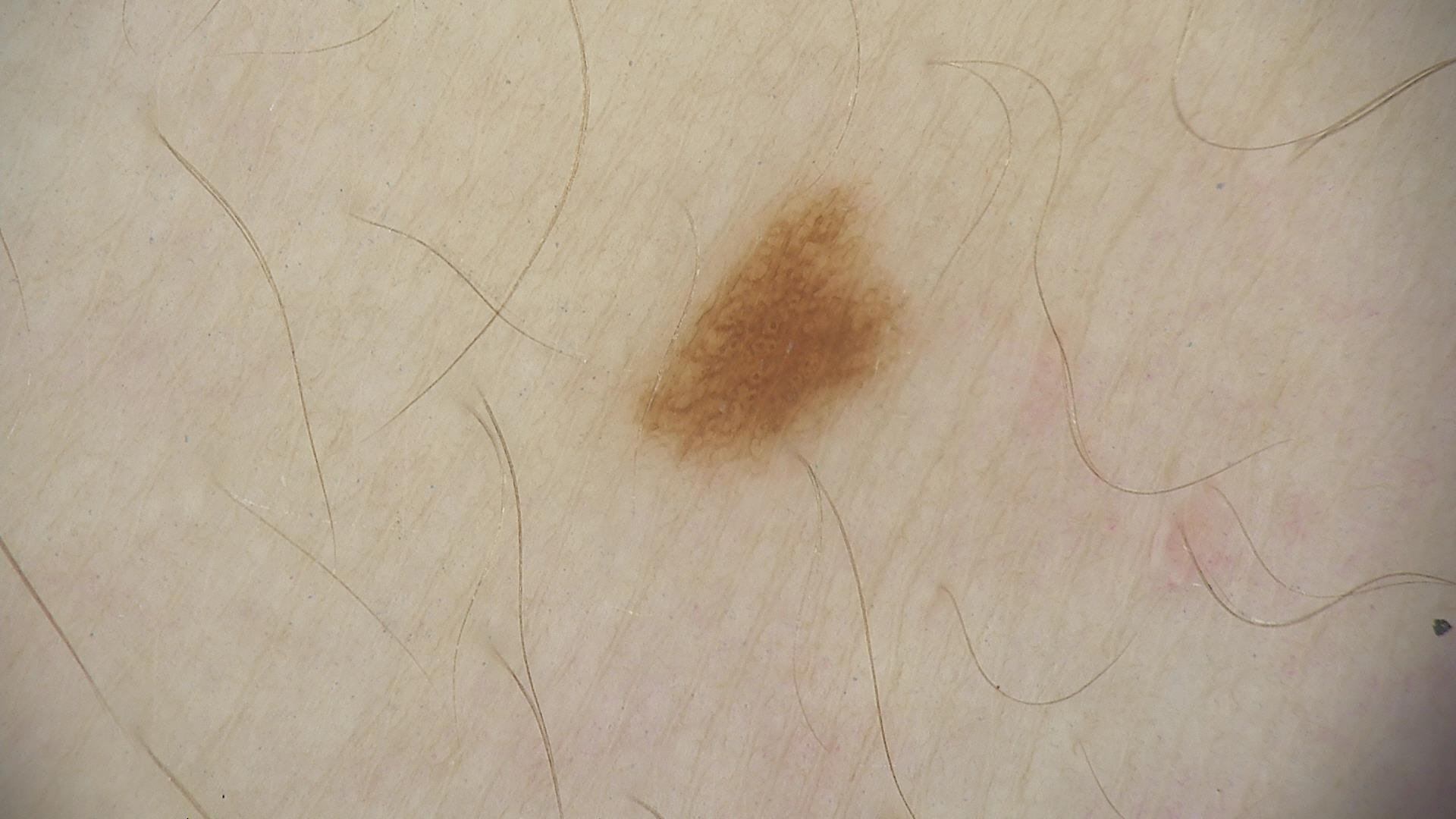Impression: Diagnosed as a junctional nevus.